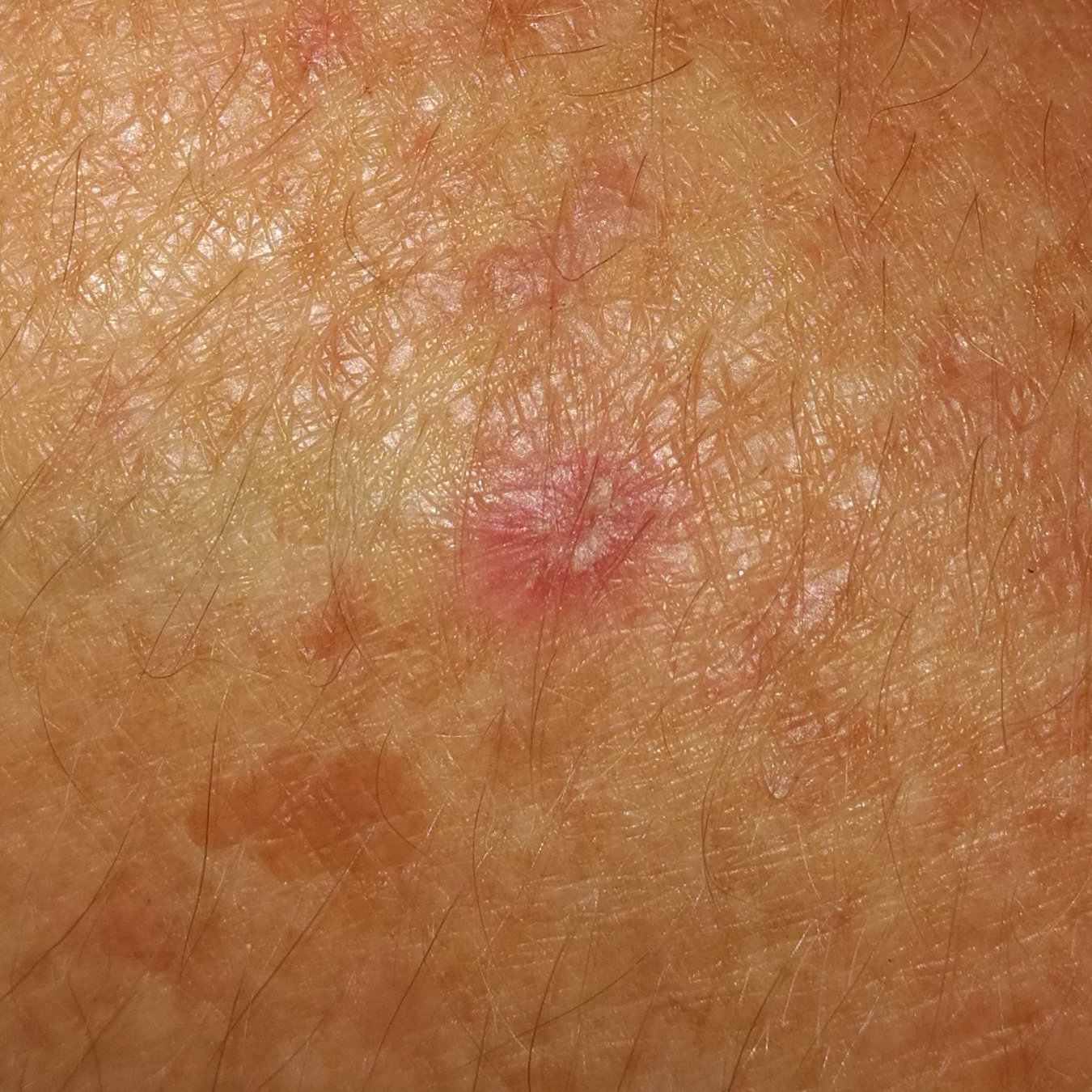A patient 52 years of age. Located on a forearm. Diagnosed by dermatologist consensus as an actinic keratosis.